A dermatoscopic image of a skin lesion:
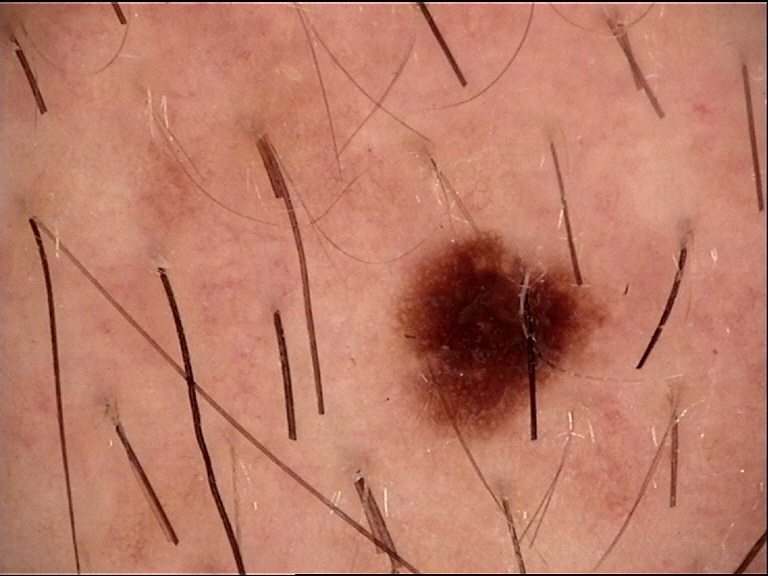<dermoscopy>
<diagnosis>
<name>dysplastic junctional nevus</name>
<code>jd</code>
<malignancy>benign</malignancy>
<super_class>melanocytic</super_class>
<confirmation>expert consensus</confirmation>
</diagnosis>
</dermoscopy>